Located on the arm and front of the torso; the photograph is a close-up of the affected area; the contributor is a female aged 18–29: 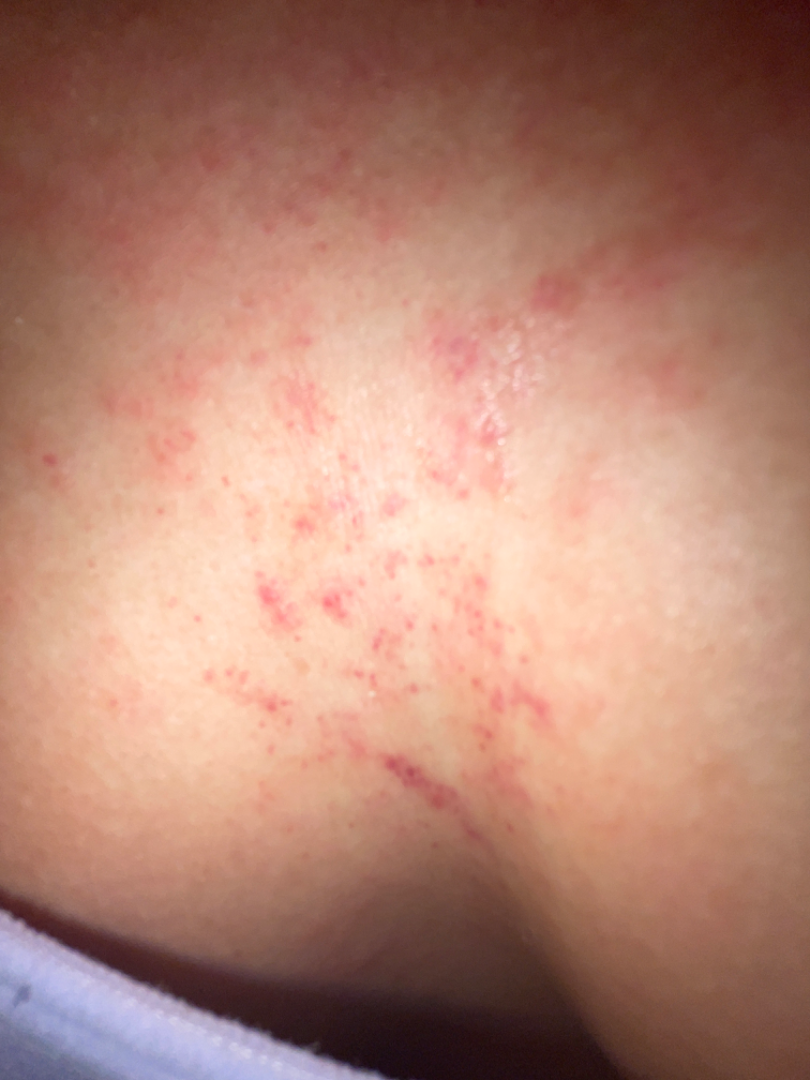differential — three dermatologists independently reviewed the case: the leading impression is Eczema; a remote consideration is Traumatic petechiae; less probable is Allergic Contact Dermatitis; less likely is Viral Exanthem; lower on the differential is Leukocytoclastic Vasculitis